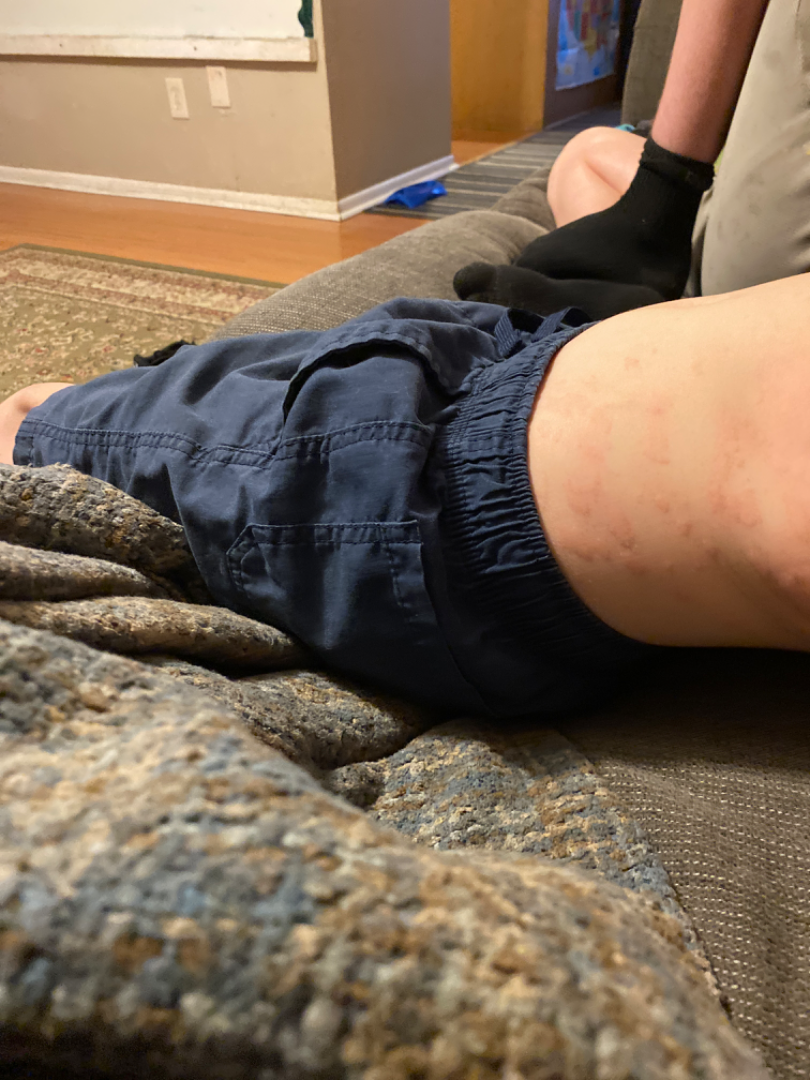An image taken at a distance. The reviewing clinician's impression was: in keeping with Urticaria.